This is a close-up image. The patient indicates enlargement and burning. Fitzpatrick skin type III; non-clinician graders estimated MST 2 or 3. Texture is reported as raised or bumpy. The lesion involves the leg — 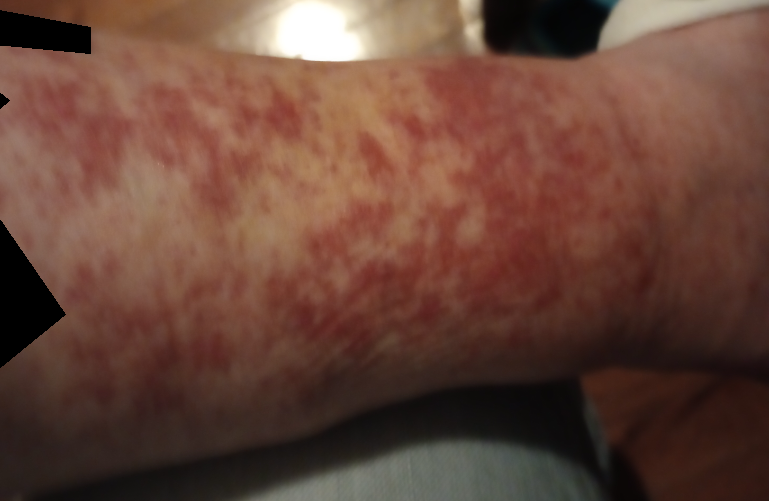The reviewing clinician's impression was: Photodermatitis (possible); Eczema (possible); Irritant Contact Dermatitis (possible).